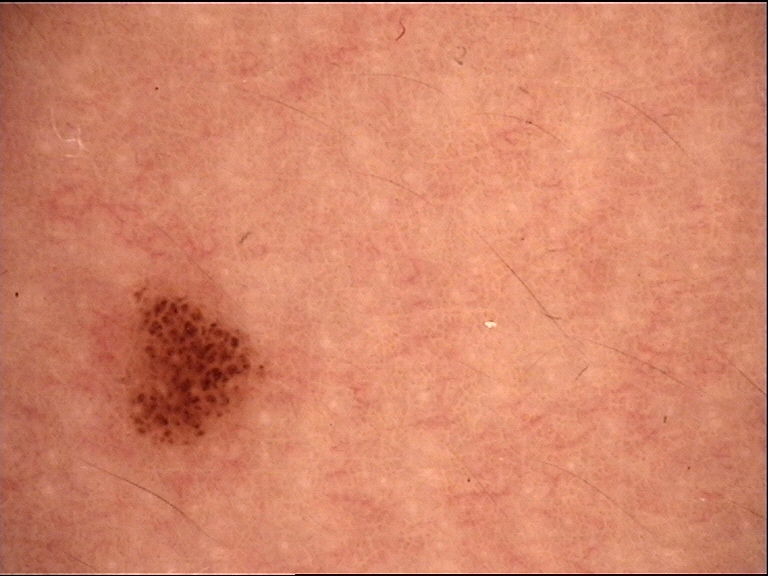  image: dermatoscopy
  lesion_type:
    main_class: banal
    pattern: compound
  diagnosis:
    name: compound nevus
    code: cb
    malignancy: benign
    super_class: melanocytic
    confirmation: expert consensus